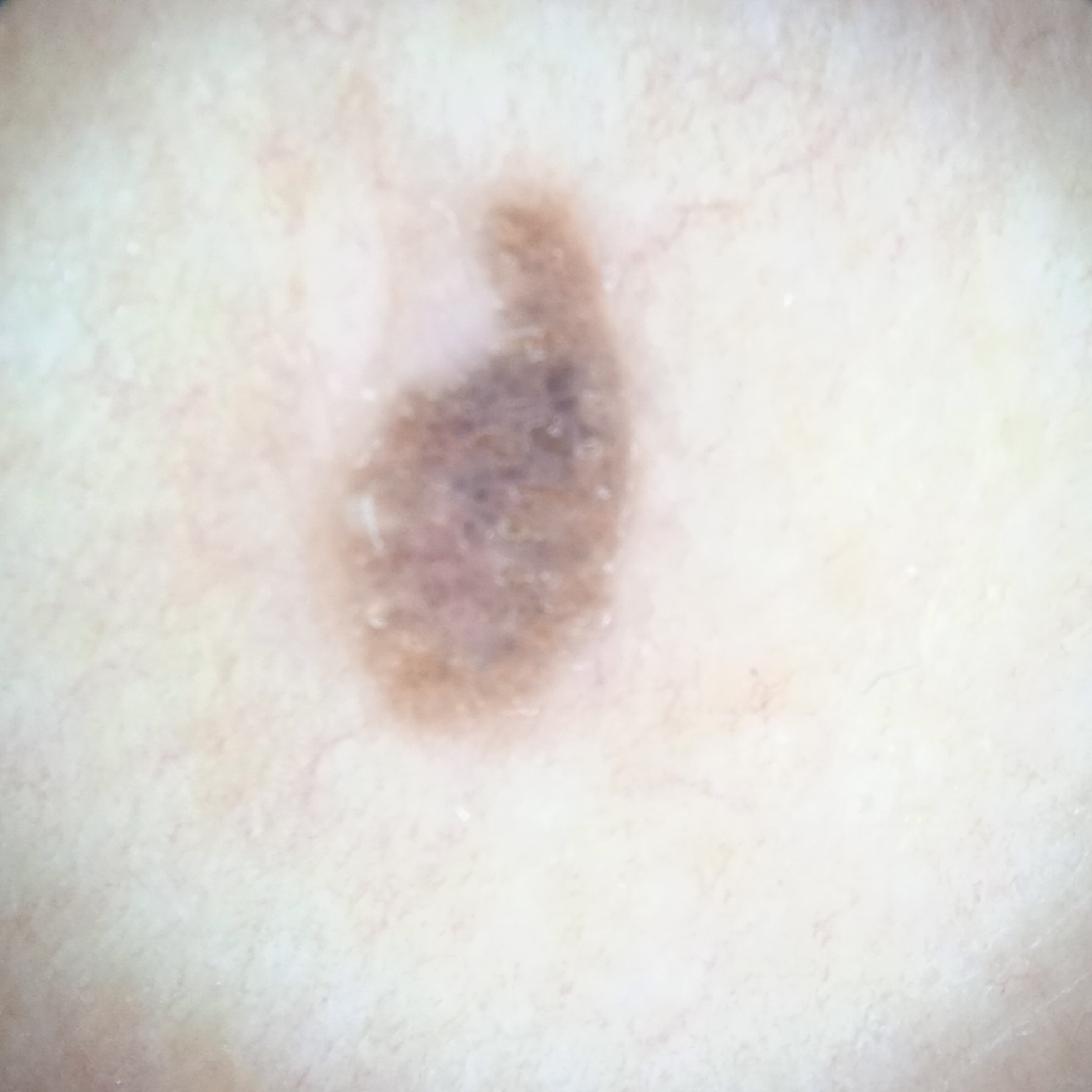Acquired for a research image collection, with no referral diagnosis. A female patient 60 years old. A dermatoscopic image of a skin lesion. The lesion is on the torso. Measuring roughly 6.2 mm. The diagnostic impression was a seborrheic keratosis.